Close-up view:
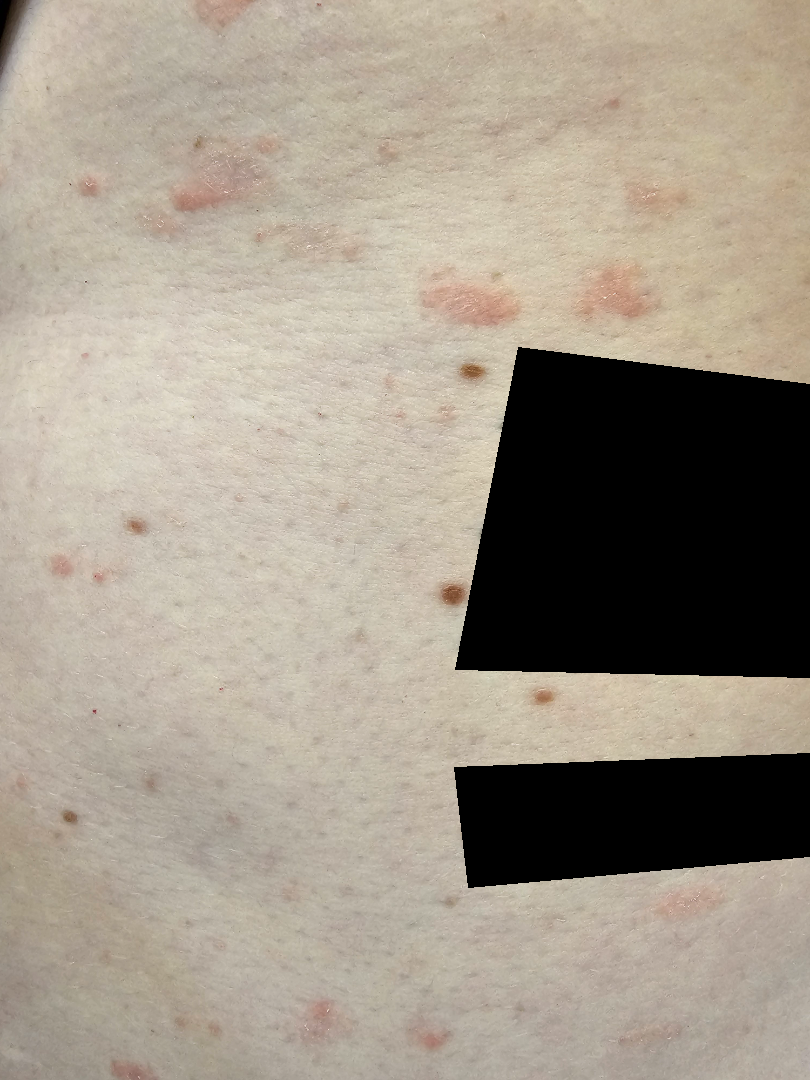Eczema (0.33); Psoriasis (0.33); Pityriasis lichenoides (0.33).